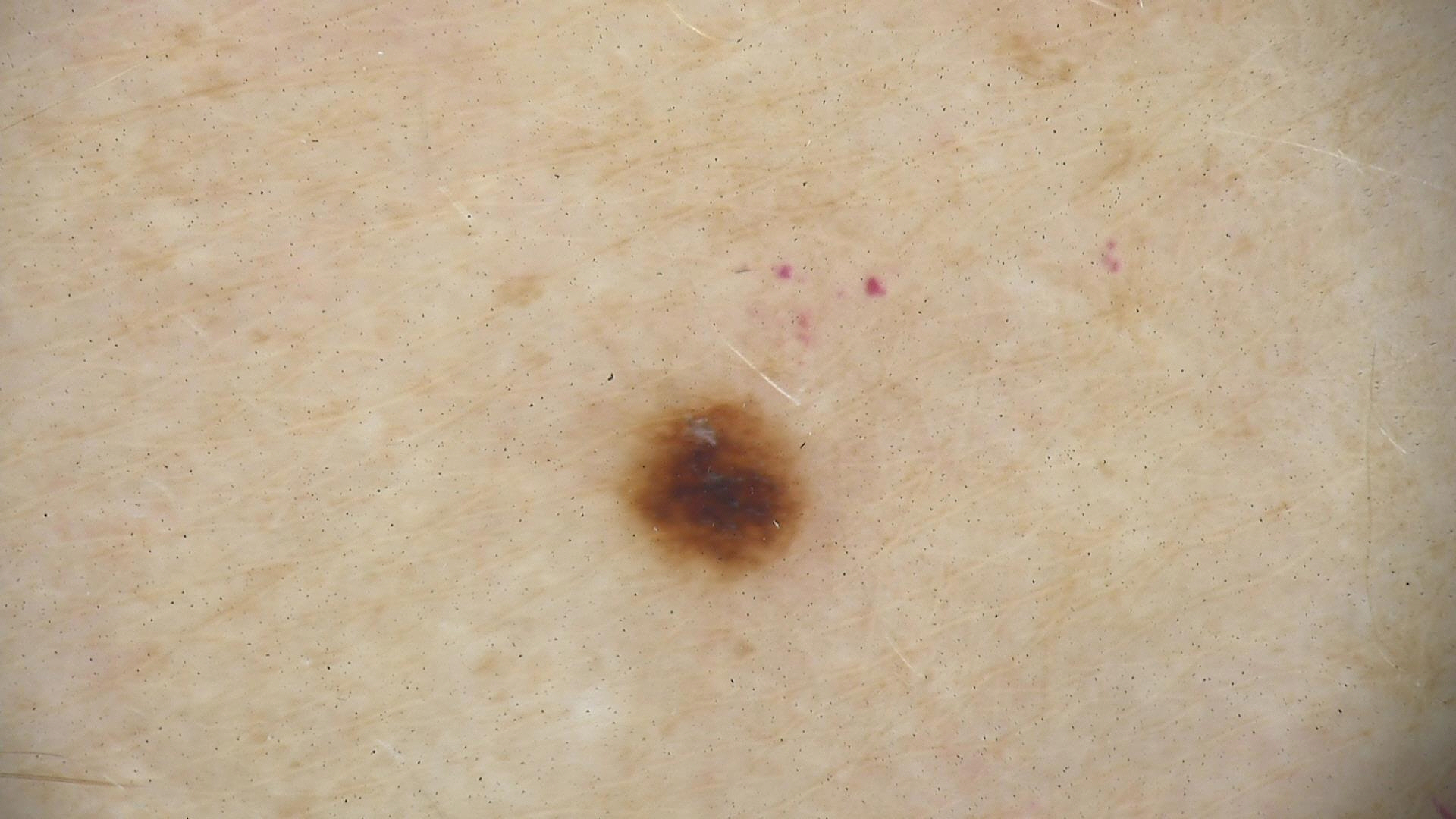{
  "image": "dermoscopy",
  "diagnosis": {
    "name": "dysplastic junctional nevus",
    "code": "jd",
    "malignancy": "benign",
    "super_class": "melanocytic",
    "confirmation": "expert consensus"
  }
}